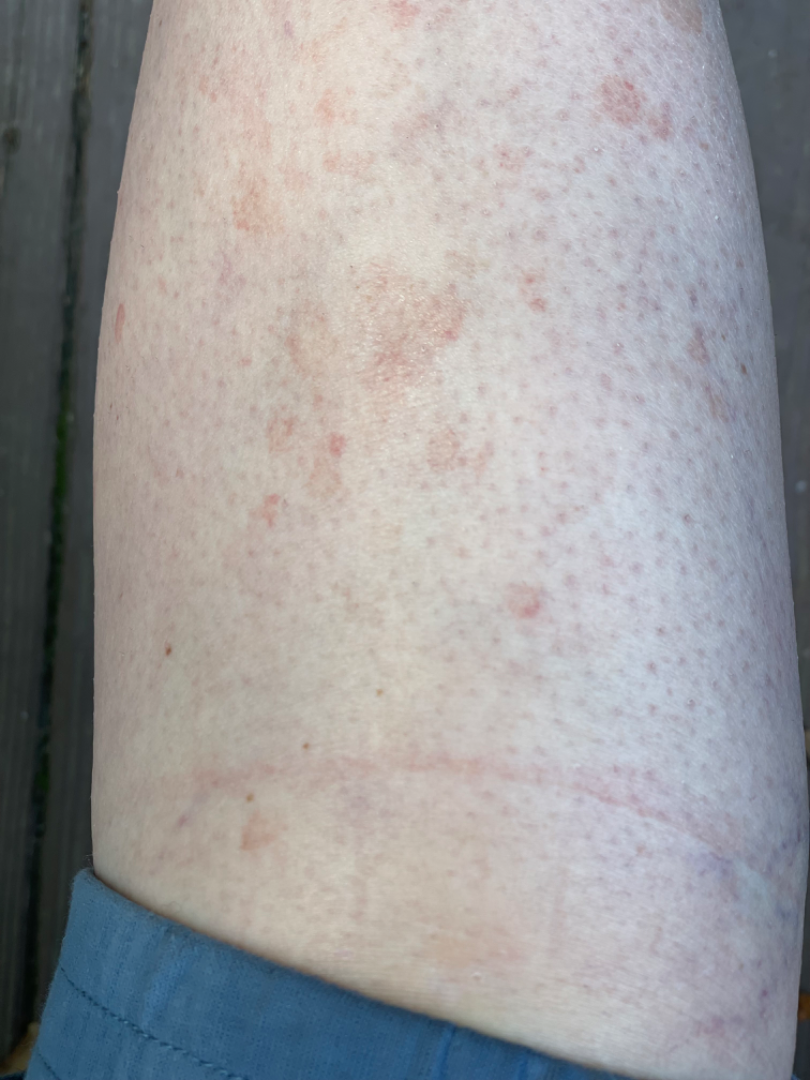assessment = unable to determine.